Dermoscopy of a skin lesion — 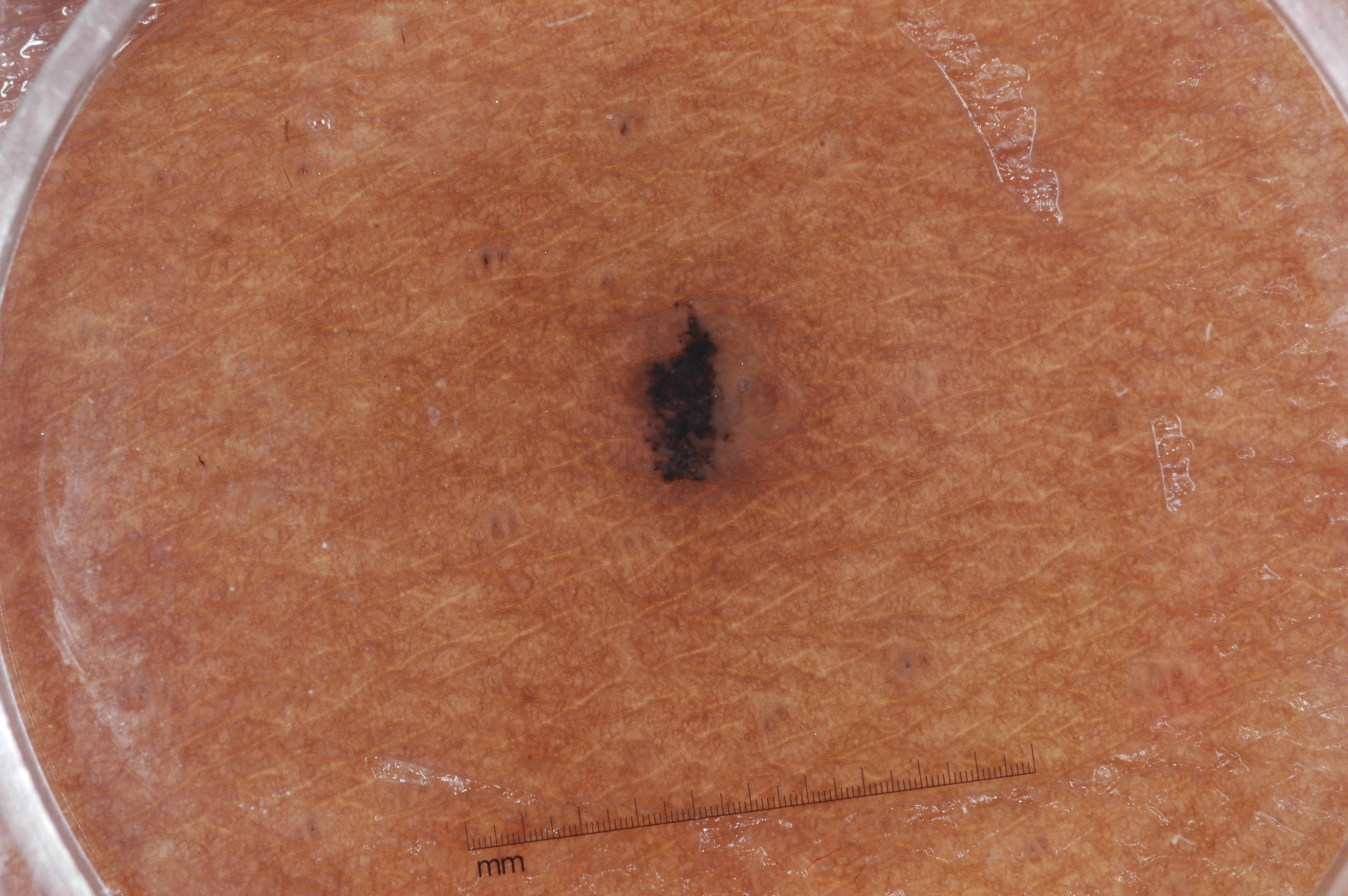Case summary:
– absent dermoscopic features: pigment network, milia-like cysts, negative network, and streaks
– extent: ~4% of the field
– lesion location: box(570, 243, 833, 539)
– impression: a melanocytic nevus, a benign lesion